A dermoscopic image of a skin lesion — 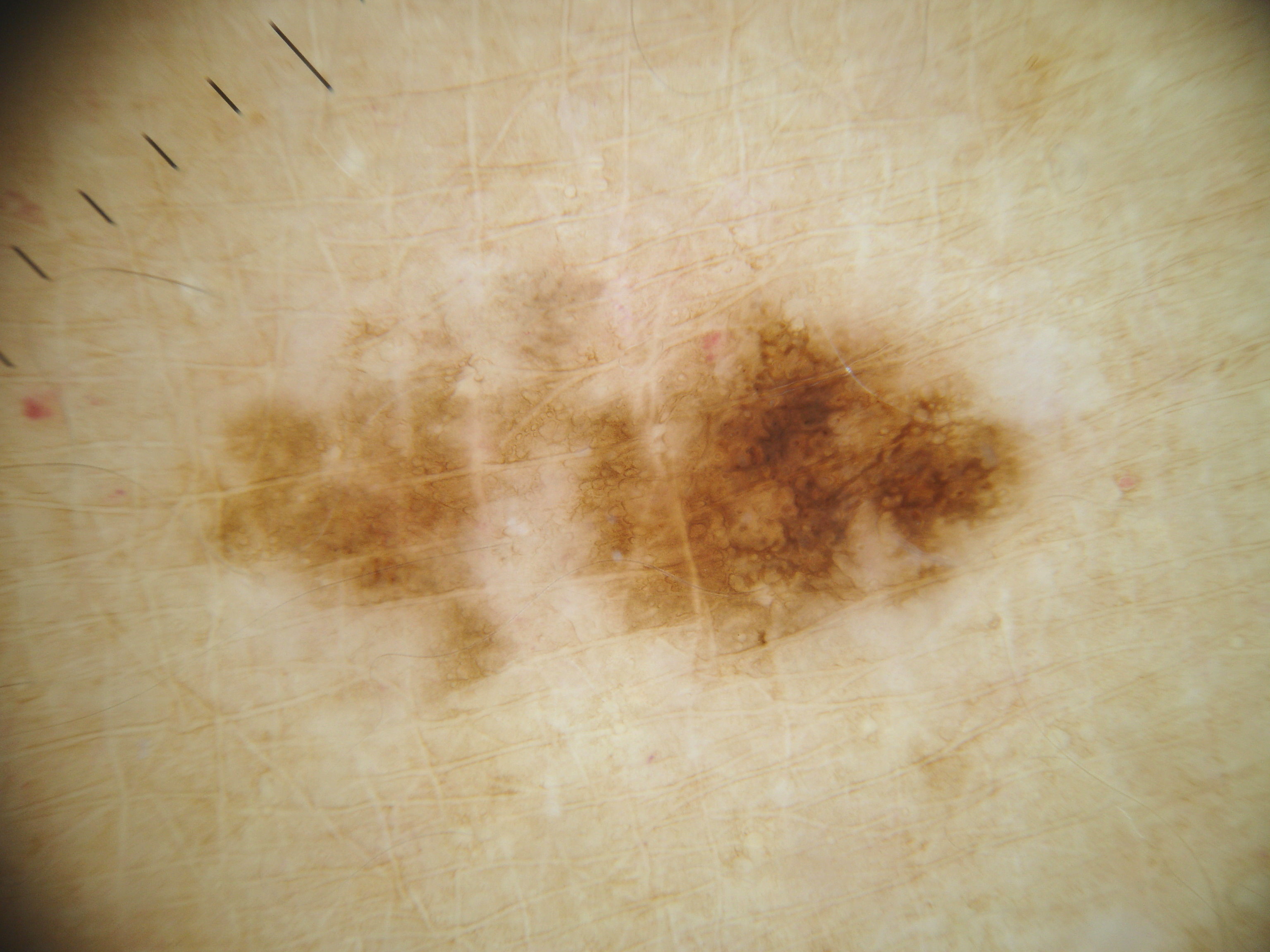Summary: Dermoscopy demonstrates globules and pigment network. Lesion location: x1=175 y1=231 x2=1042 y2=721. Conclusion: On biopsy, the diagnosis was a melanoma, a malignant lesion.